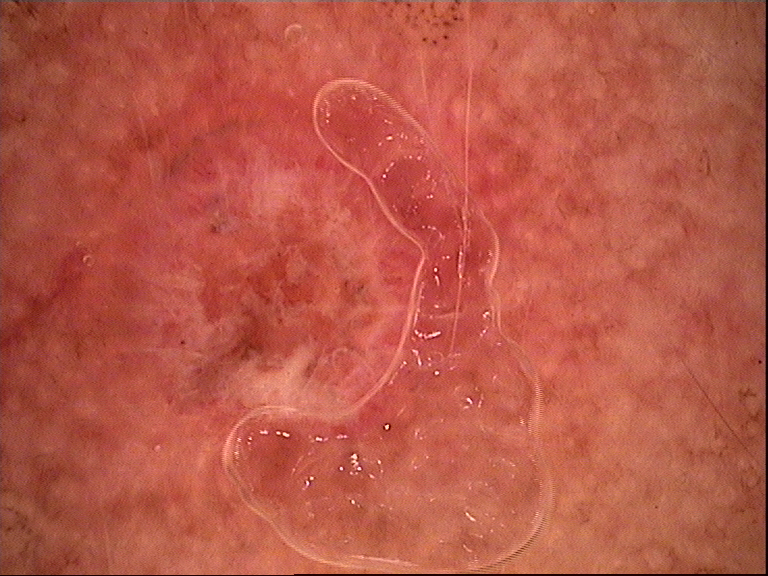A dermoscopic close-up of a skin lesion.
Biopsy-confirmed as a keratinocytic, malignant lesion — a basal cell carcinoma.